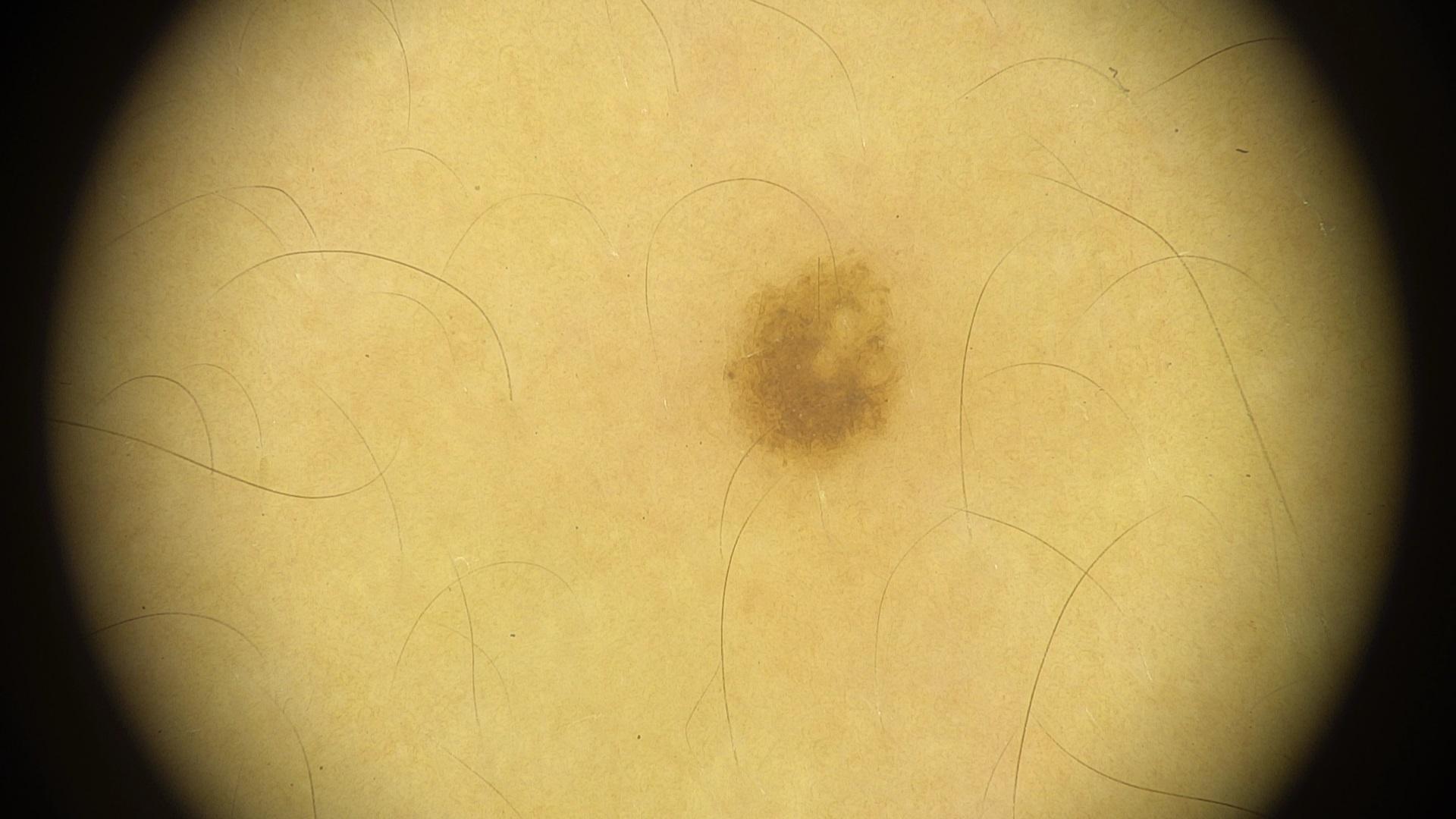A skin lesion imaged with contact-polarized dermoscopy. The patient was assessed as Fitzpatrick II. A female subject in their mid-20s. The lesion involves the trunk. The diagnostic impression was a melanocytic lesion — a nevus.